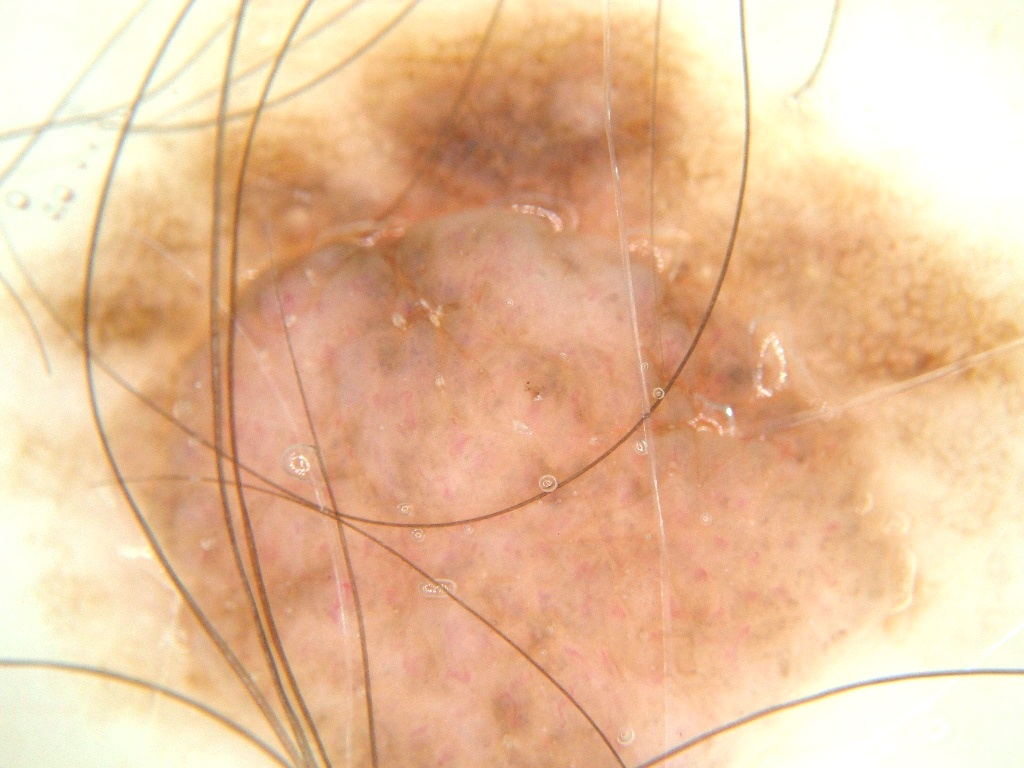A dermoscopic view of a skin lesion. The lesion reaches across nearly the entire image. Expert review diagnosed this as a benign skin lesion.